A dermoscopic image of a skin lesion:
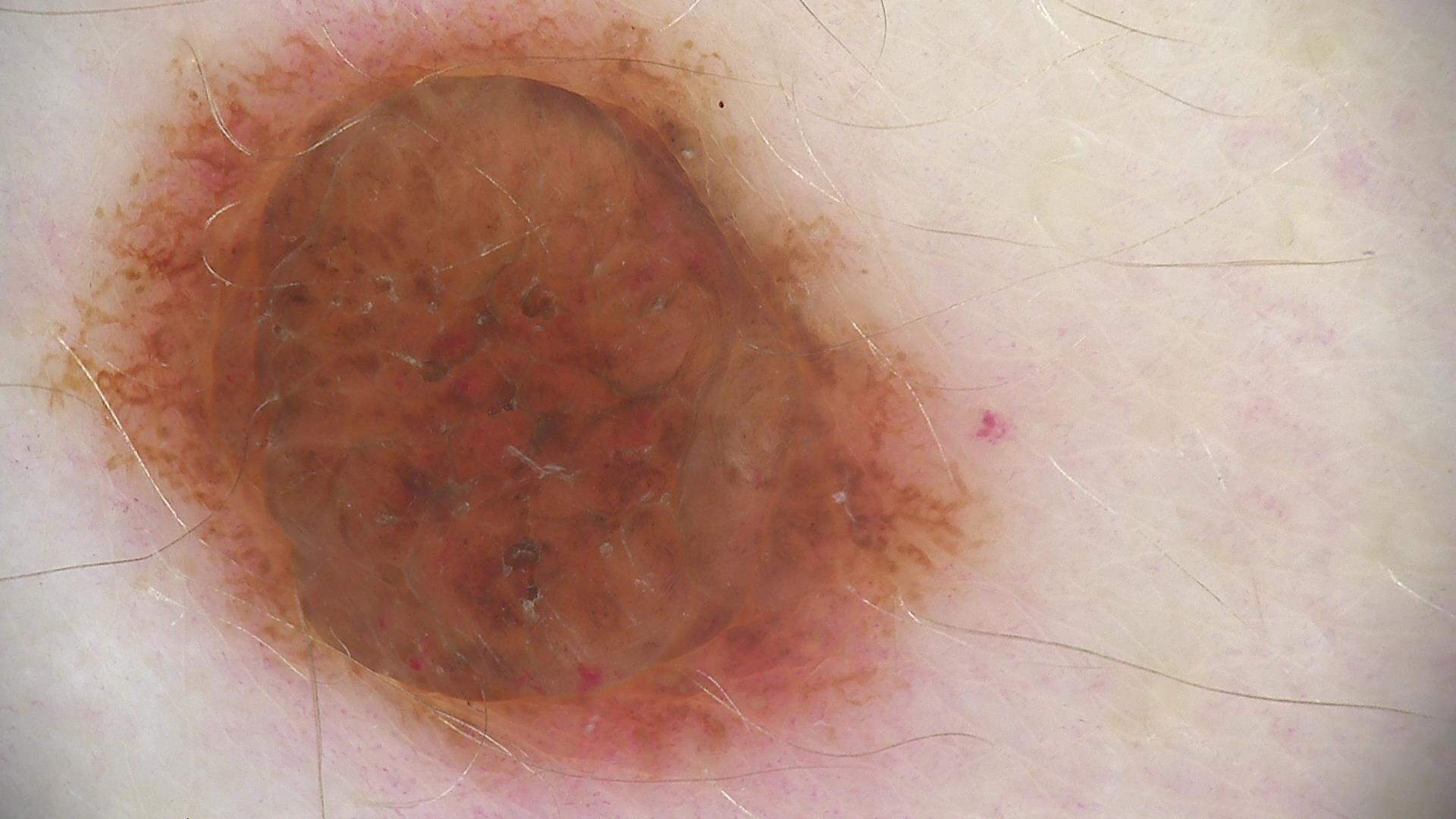Classified as a banal lesion — a dermal nevus.